The patient is male; this image was taken at a distance; the lesion involves the back of the hand: 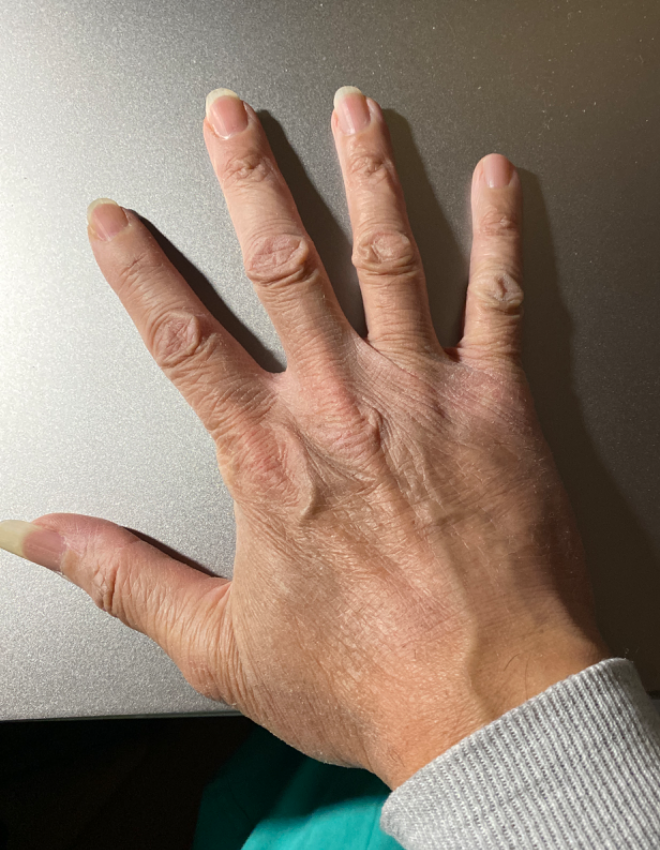<report>
  <texture>flat, rough or flaky</texture>
  <systemic_symptoms>none reported</systemic_symptoms>
  <duration>three to twelve months</duration>
  <skin_tone>
    <fitzpatrick>III</fitzpatrick>
  </skin_tone>
  <differential>
    <tied_lead>Eczema, Xerosis</tied_lead>
    <considered>Tinea</considered>
  </differential>
</report>